A dermoscopic close-up of a skin lesion.
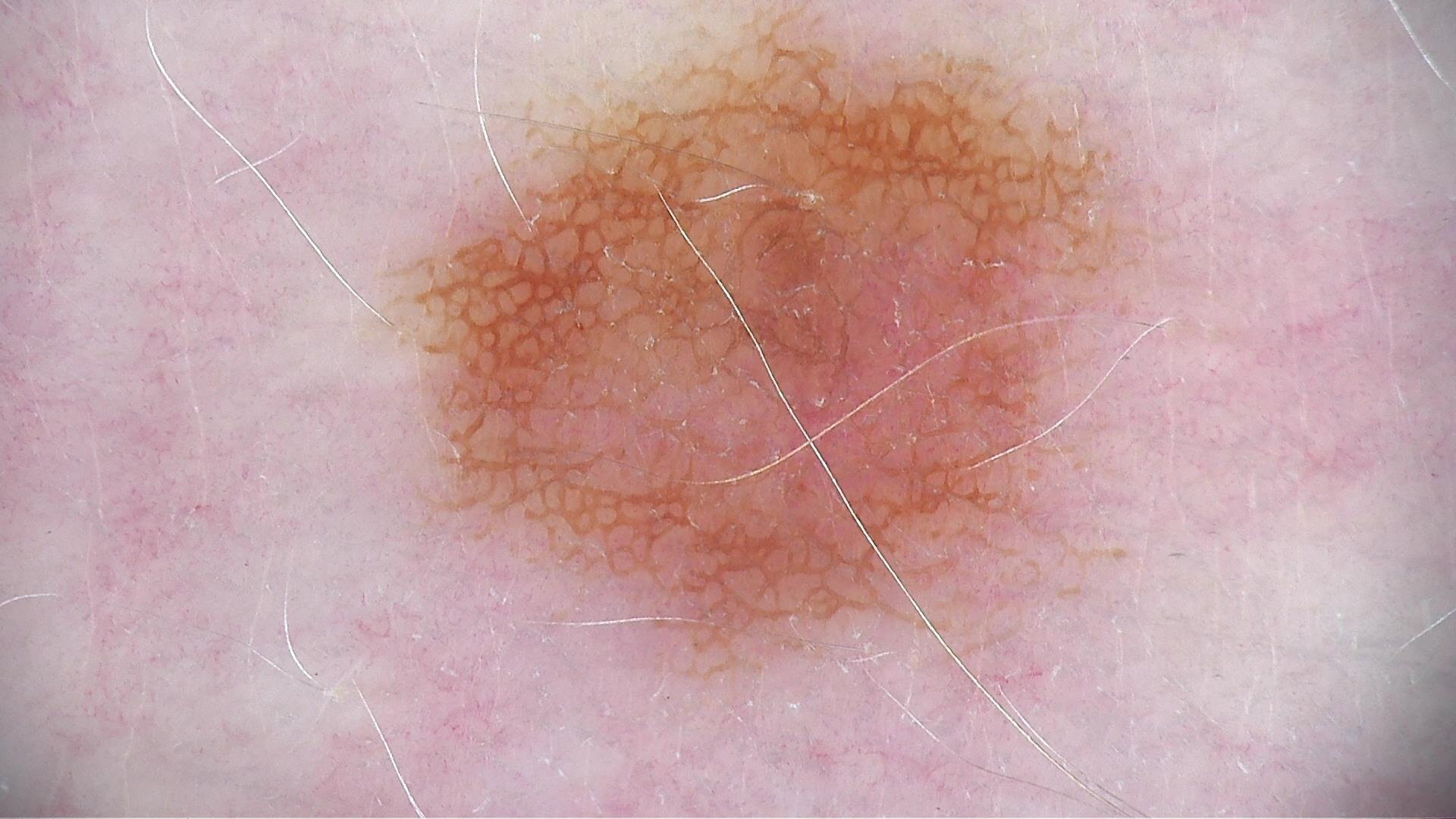diagnostic label=dysplastic junctional nevus (expert consensus).